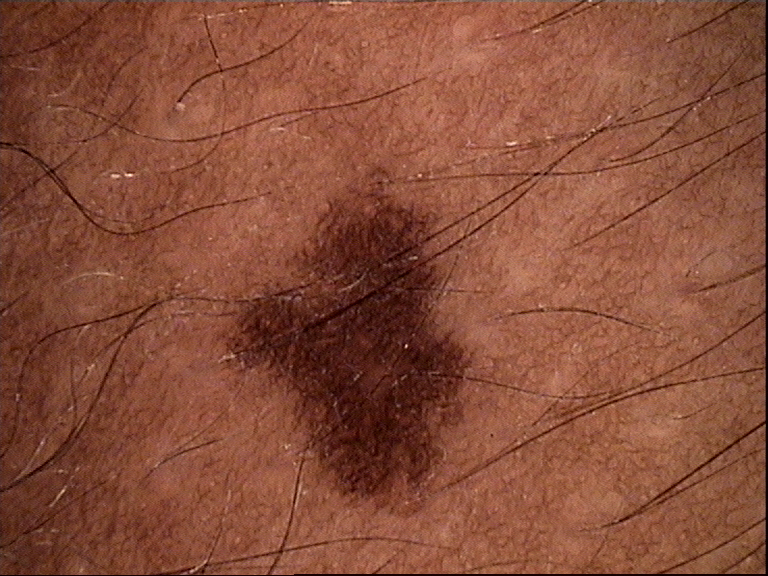image type=dermoscopy
diagnosis=dysplastic junctional nevus (expert consensus)